A dermoscopic photograph of a skin lesion: 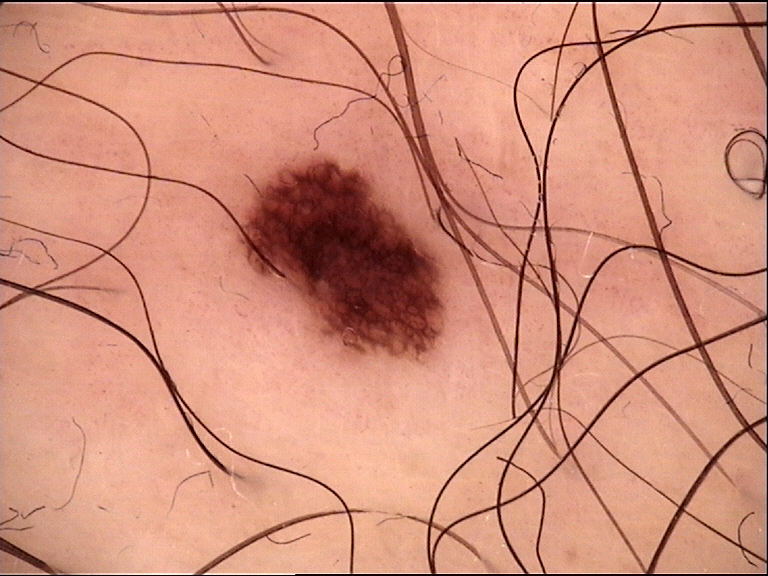The architecture is that of a banal lesion.
Labeled as a junctional nevus.